This is a dermoscopic photograph of a skin lesion, the patient is a female aged approximately 30: 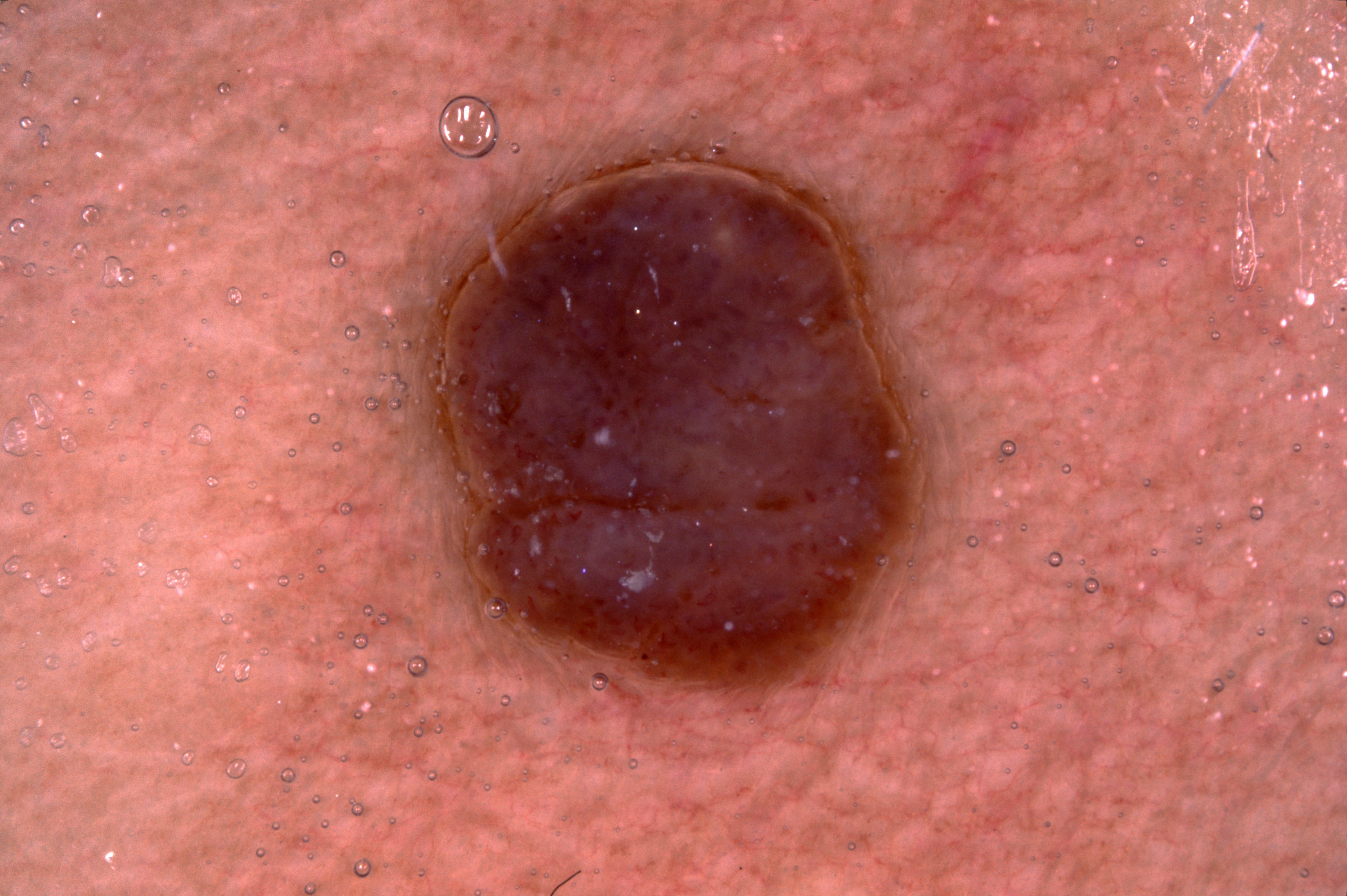Dermoscopy demonstrates milia-like cysts; no streaks, pigment network, or negative network. As (left, top, right, bottom), the lesion is located at 411, 154, 926, 700. The diagnostic assessment was a seborrheic keratosis, a benign skin lesion.